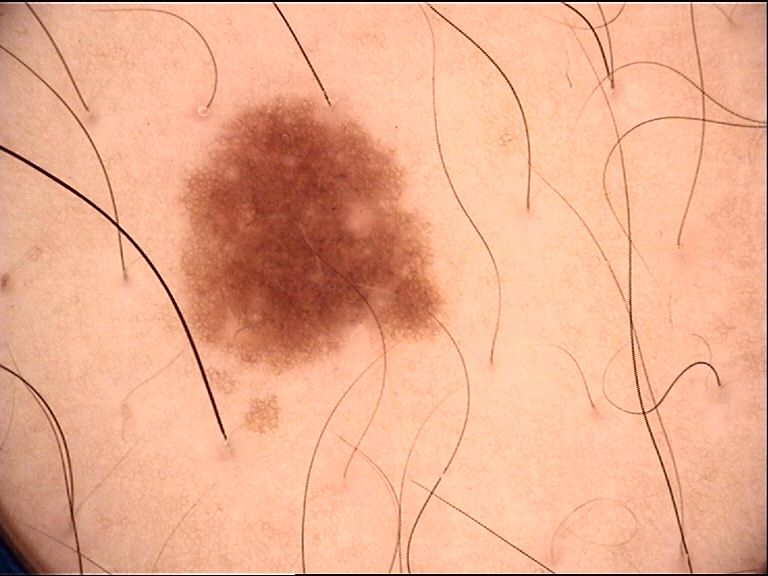The diagnostic label was a dysplastic junctional nevus.